A close-up photograph; the affected area is the leg:
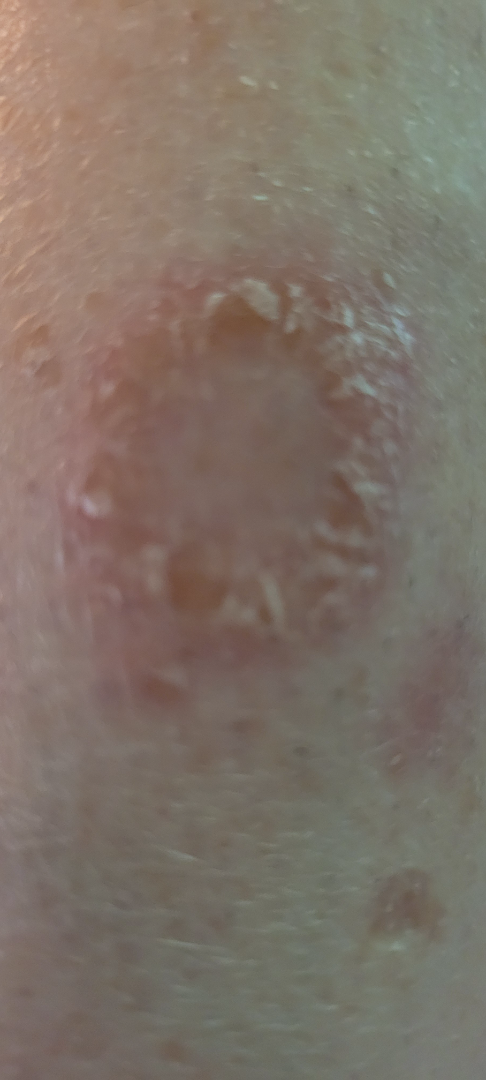Findings:
– assessment — could not be assessed
– texture — rough or flaky and raised or bumpy
– symptoms — bothersome appearance and enlargement
– other reported symptoms — fatigue, chills, mouth sores and joint pain
– onset — more than one year